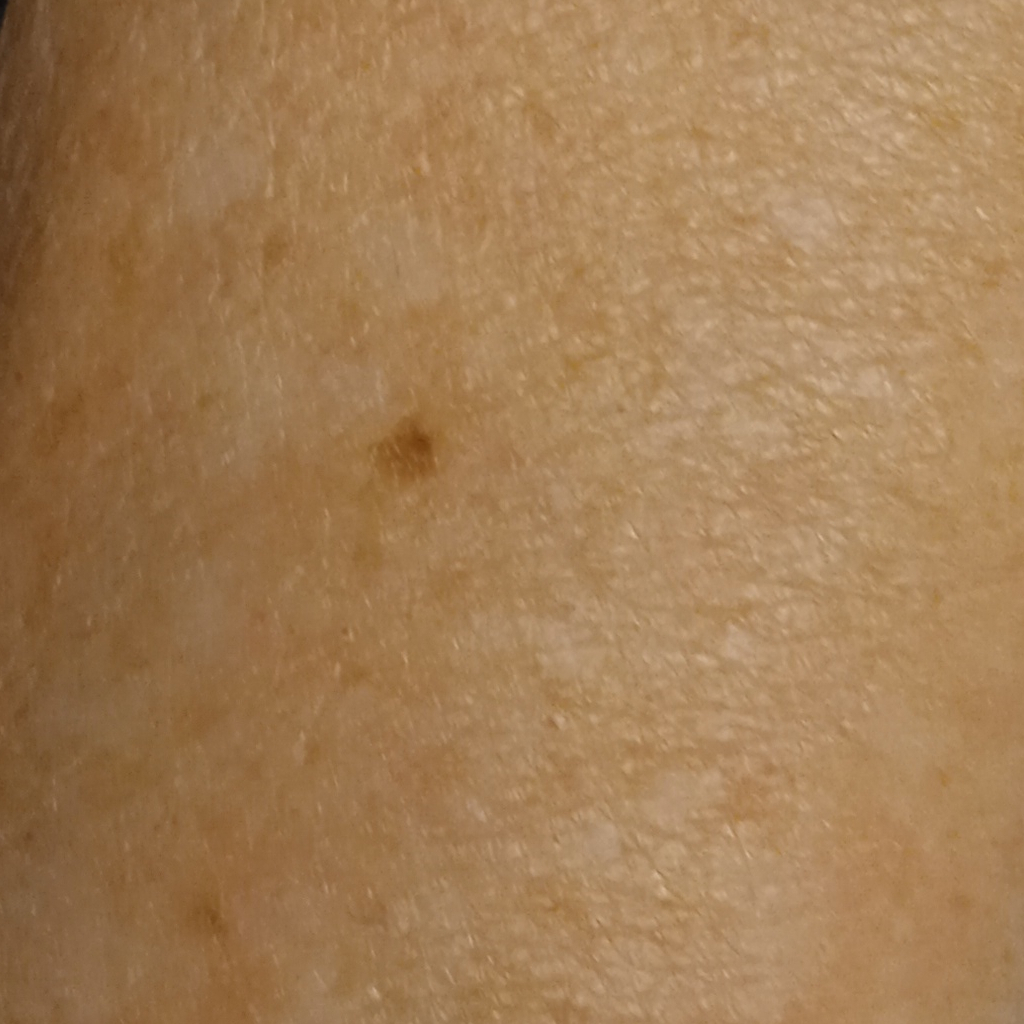The dermatologists' assessment was a melanocytic nevus.